A dermoscopic photograph of a skin lesion.
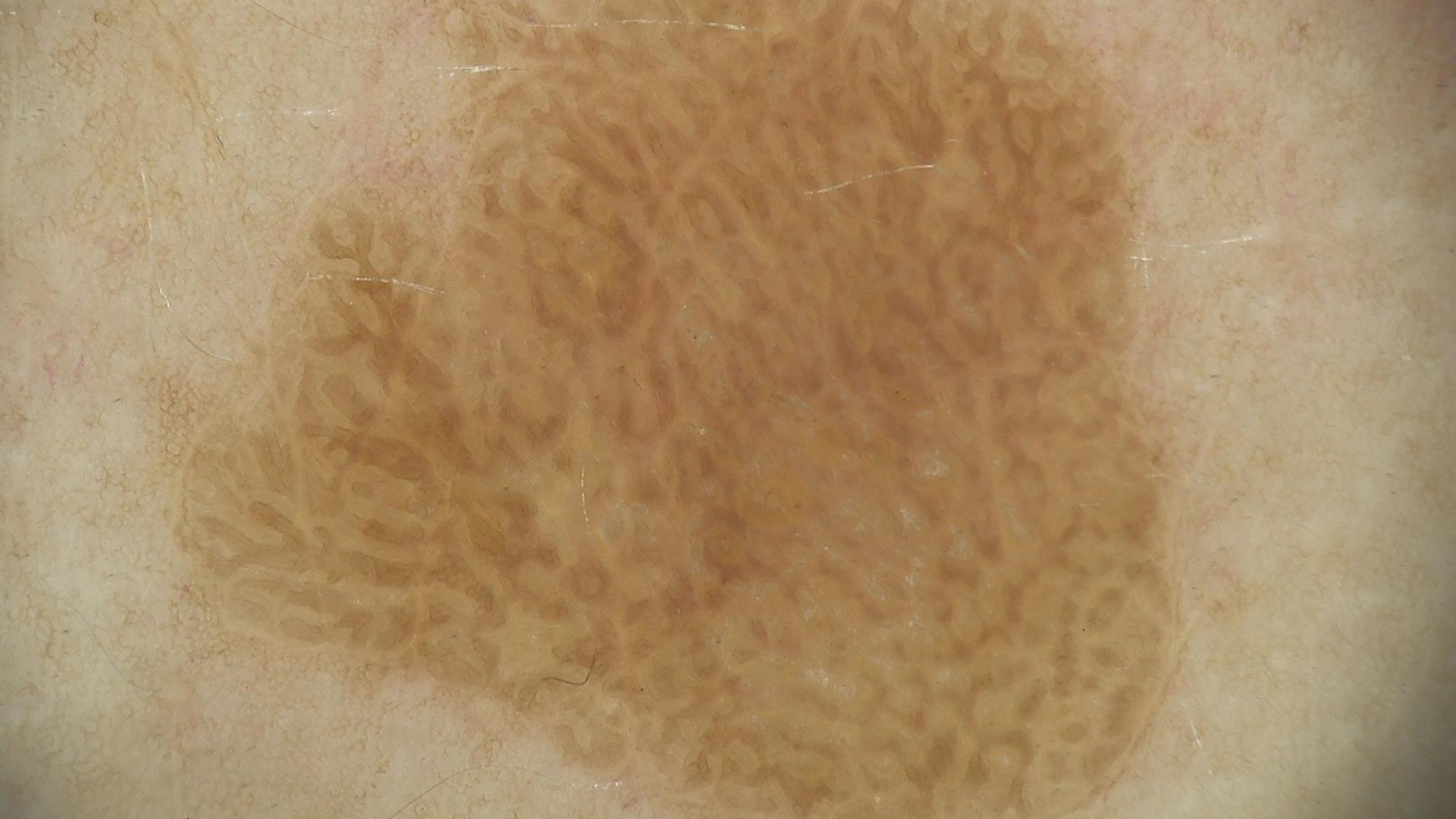This is a keratinocytic lesion.
Consistent with a seborrheic keratosis.